The patient reported no systemic symptoms. The lesion is described as raised or bumpy. An image taken at an angle. The patient is a male aged 18–29. Located on the top or side of the foot:
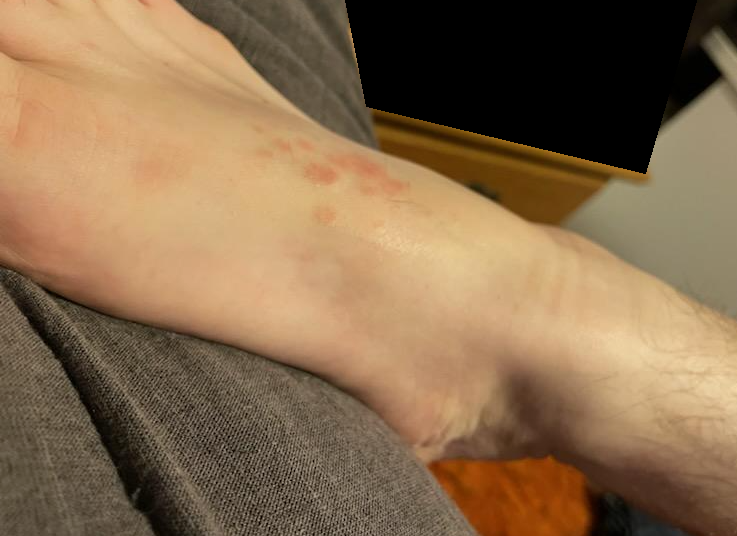Case summary:
- dermatologist impression · the differential, in no particular order, includes Eczema, Allergic Contact Dermatitis and Irritant Contact Dermatitis